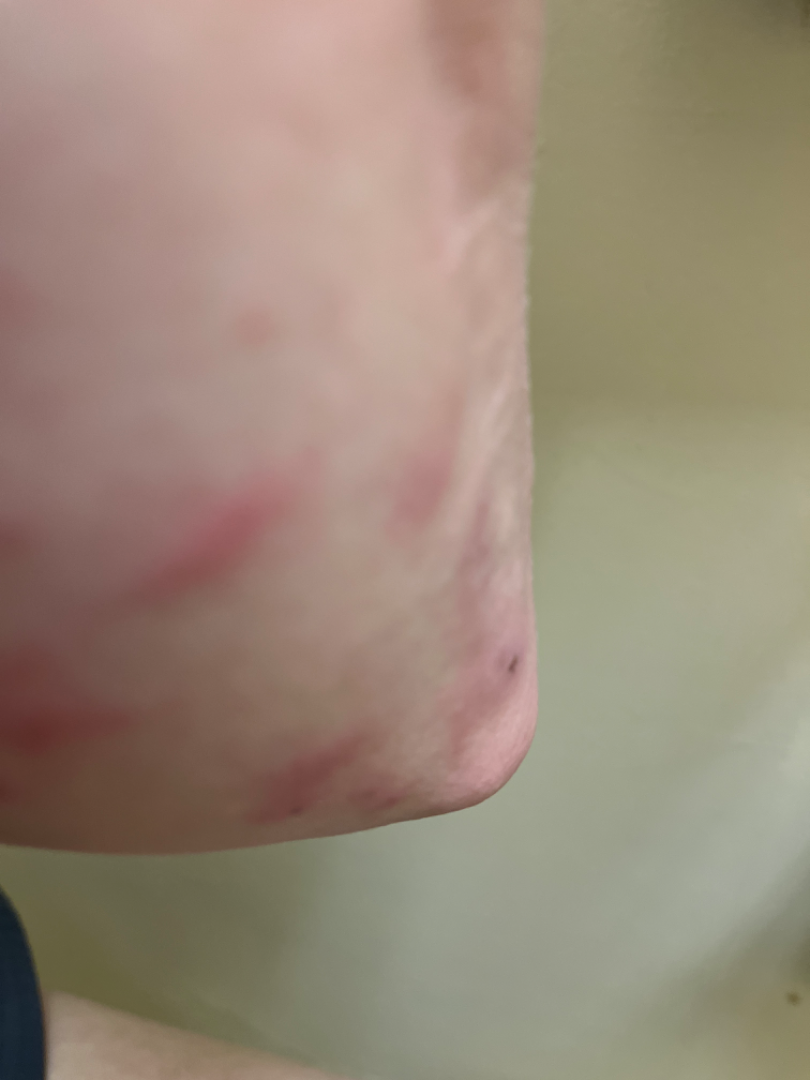Case summary:
– assessment — ungradable on photographic review
– view — close-up
– texture — raised or bumpy
– duration — less than one week
– body site — head or neck and arm